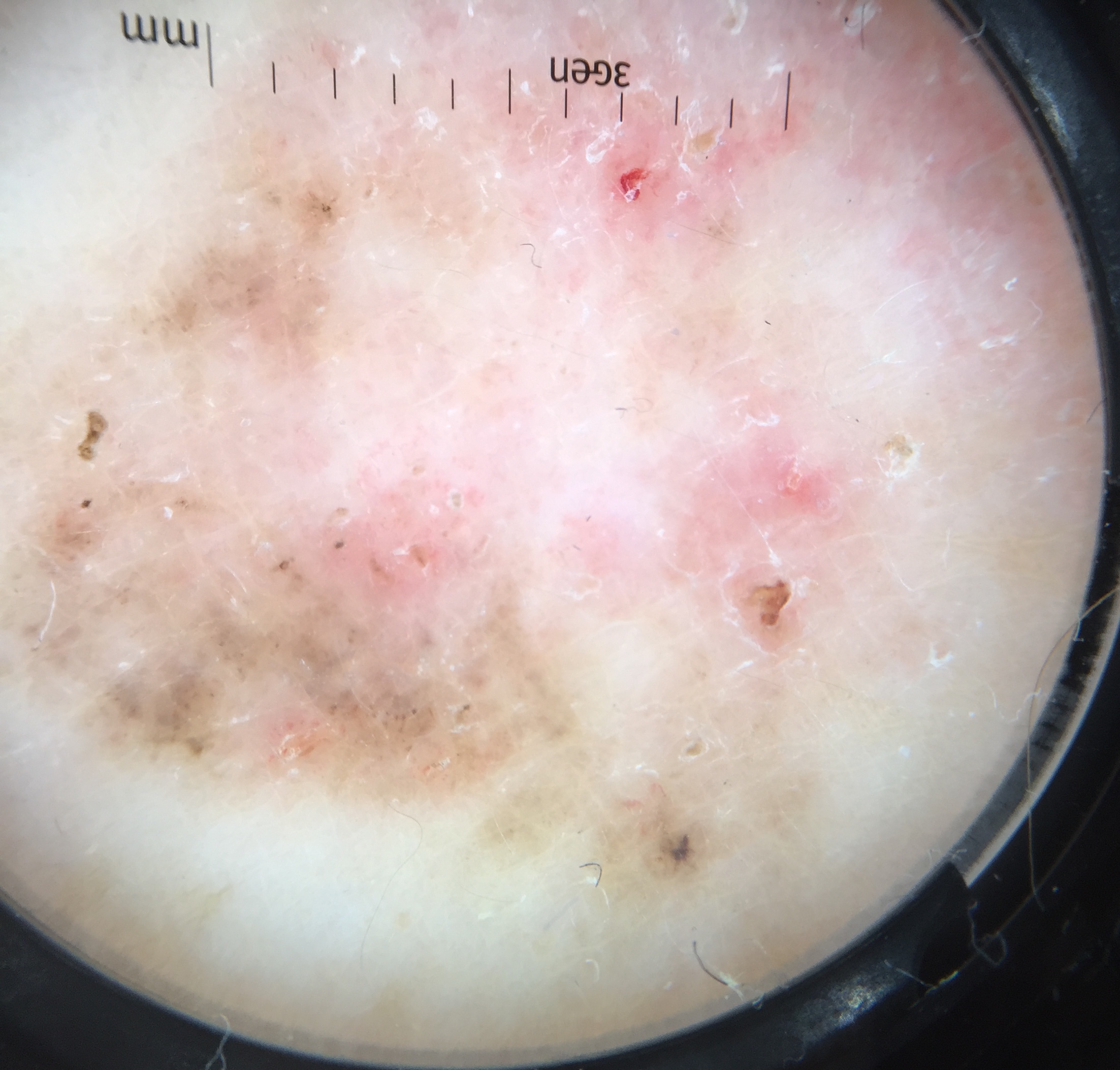image = dermatoscopy; class = basal cell carcinoma (biopsy-proven).